Recorded as Fitzpatrick skin type II. A clinical photo of a skin lesion taken with a smartphone. A male patient in their late 40s. The chart records alcohol use, prior malignancy (patient or family), pesticide exposure, and prior skin cancer (patient or family) — 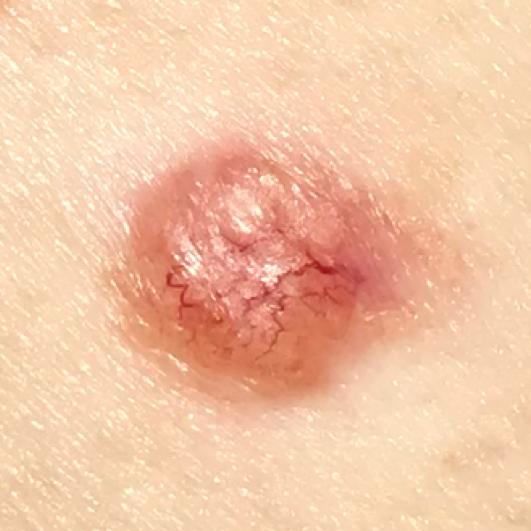Located on the face.
The lesion measures approximately 7 × 6 mm.
By the patient's account, the lesion has bled, is elevated, and has grown, but does not itch.
Biopsy-confirmed as a basal cell carcinoma.